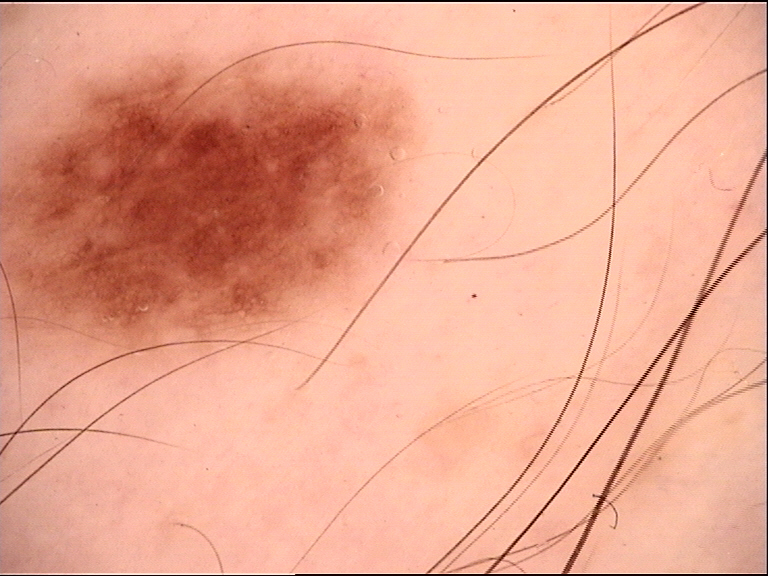Consistent with a benign lesion — a dysplastic junctional nevus.